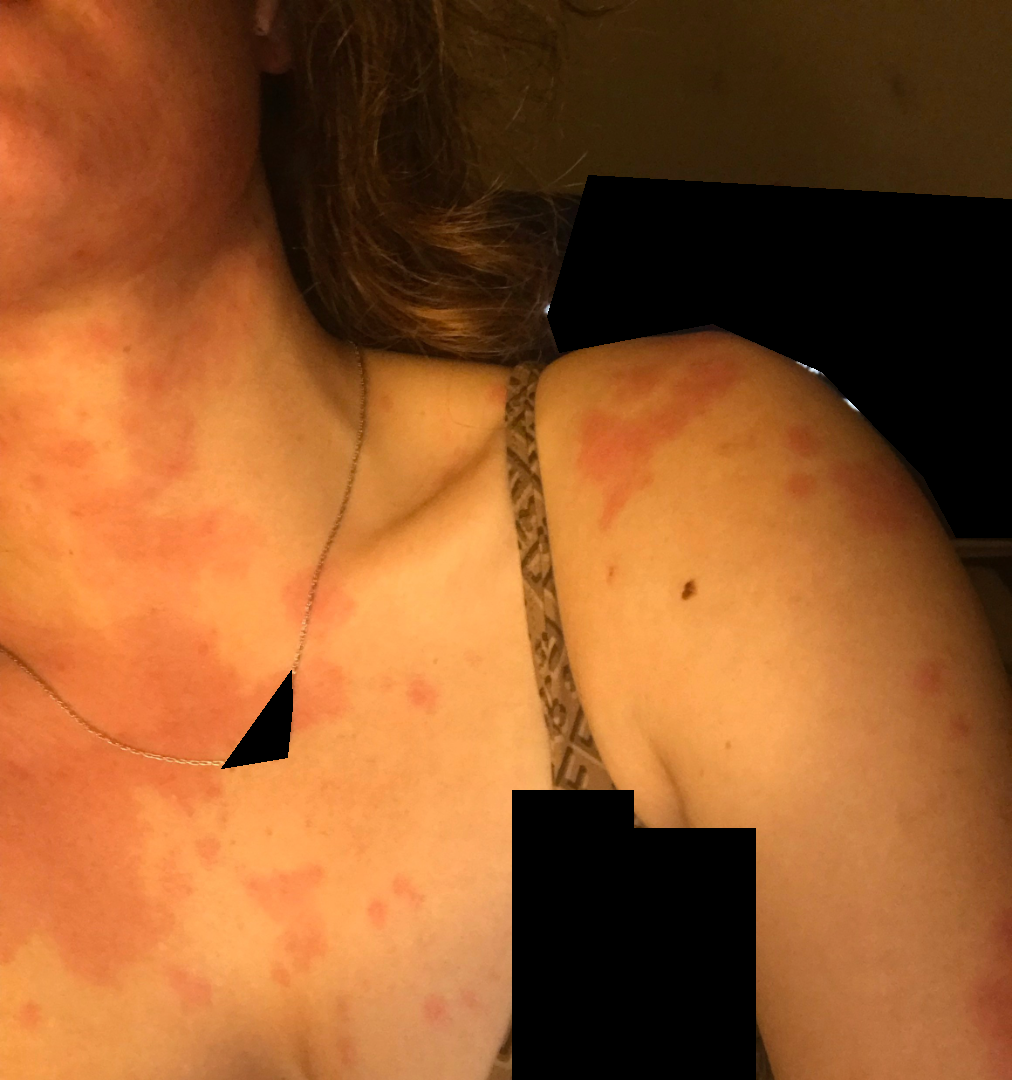The case was indeterminate on photographic review. This is a close-up image. The back of the torso, back of the hand, head or neck, arm and front of the torso are involved.